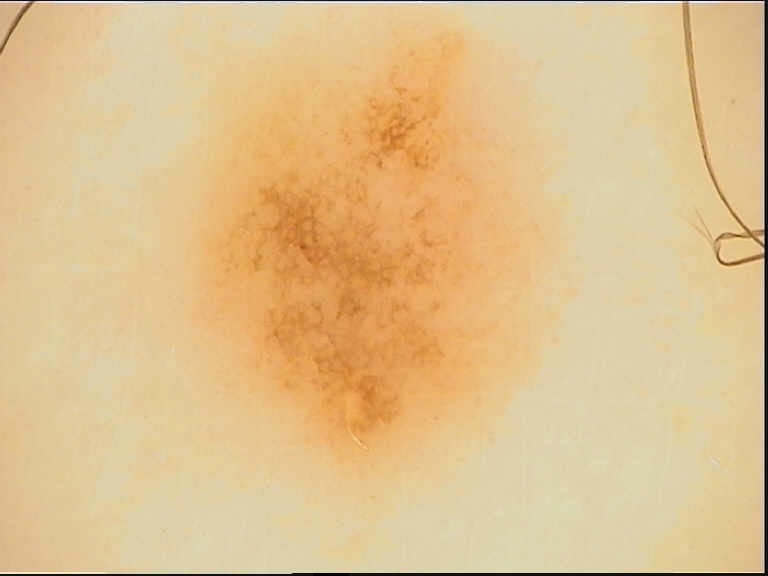{"diagnosis": {"name": "dysplastic junctional nevus", "code": "jd", "malignancy": "benign", "super_class": "melanocytic", "confirmation": "expert consensus"}}